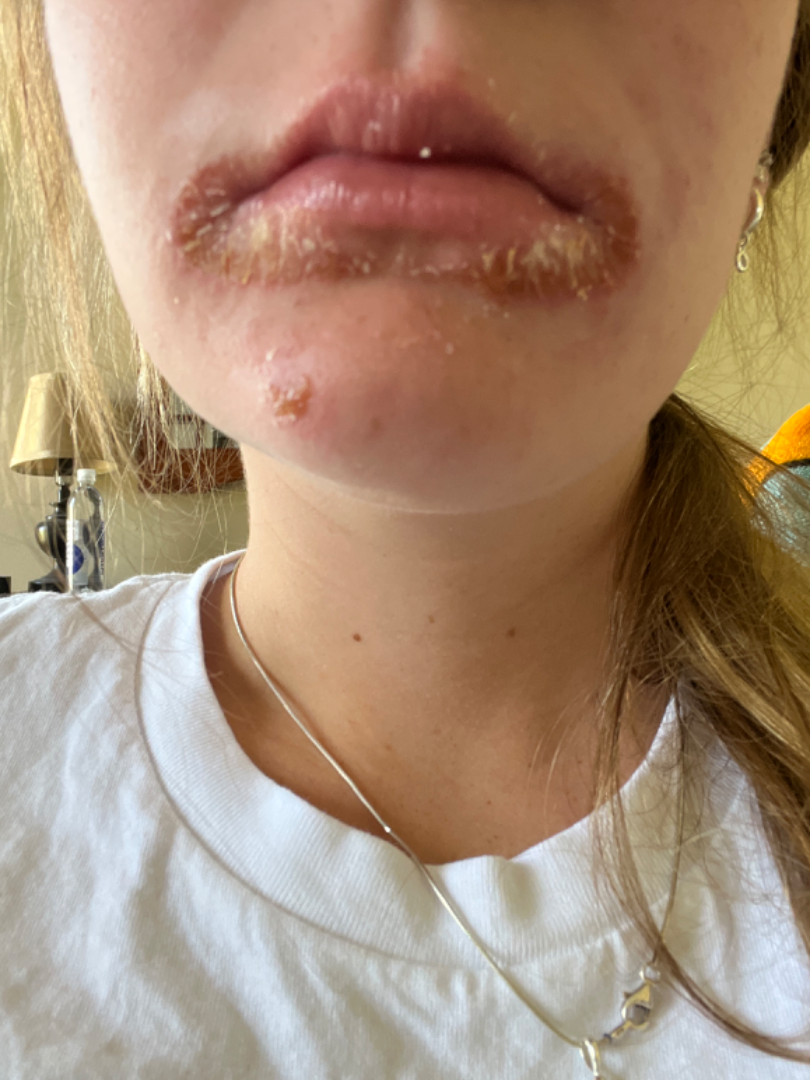Skin tone: Fitzpatrick skin type II; lay reviewers estimated MST 2 or 3.
Close-up view.
The patient reports darkening, enlargement and bothersome appearance.
The head or neck is involved.
Texture is reported as rough or flaky.
Consistent with Impetigo.